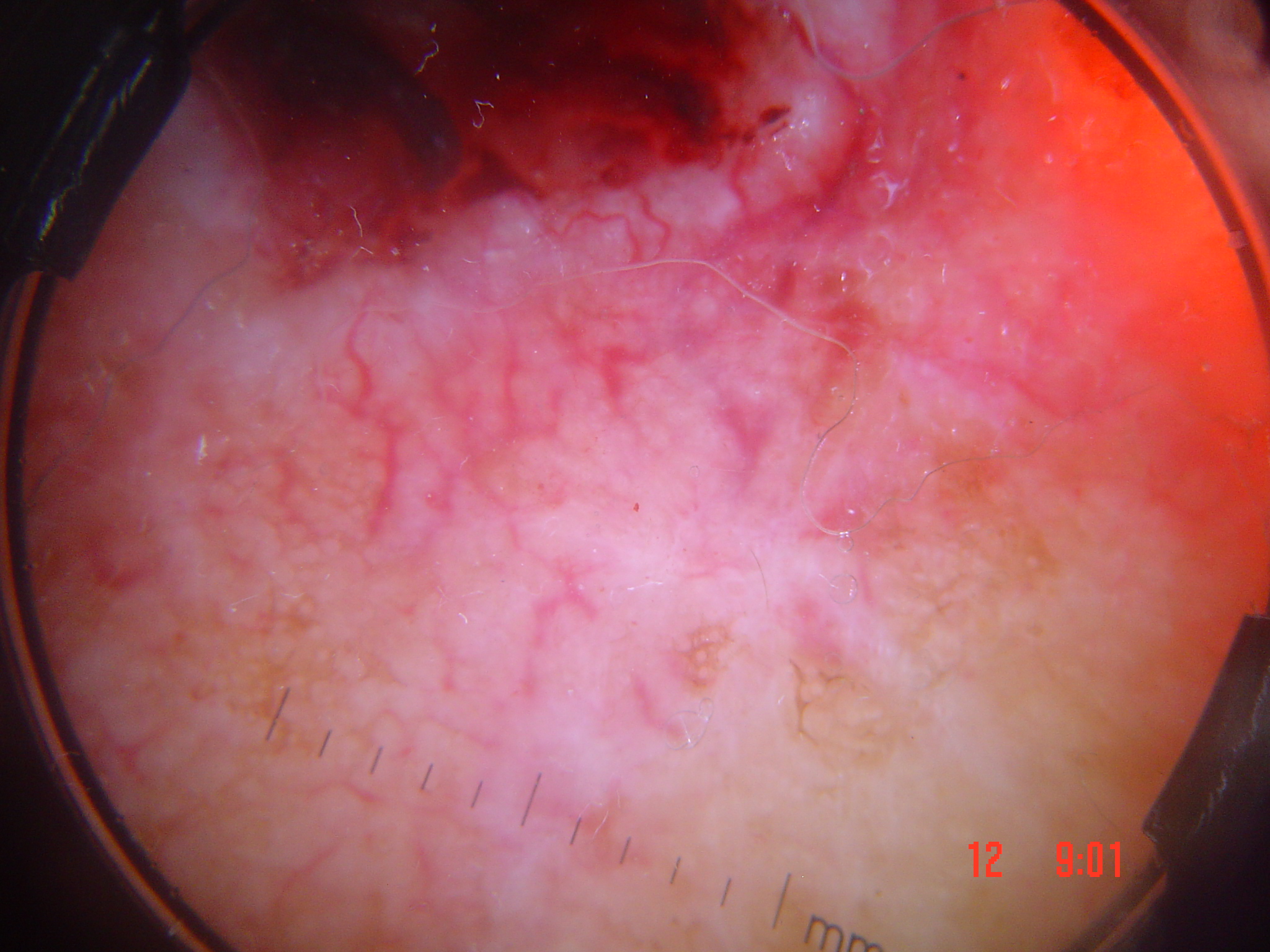Findings:
– imaging · dermoscopy
– category · keratinocytic
– diagnostic label · squamous cell carcinoma (biopsy-proven)